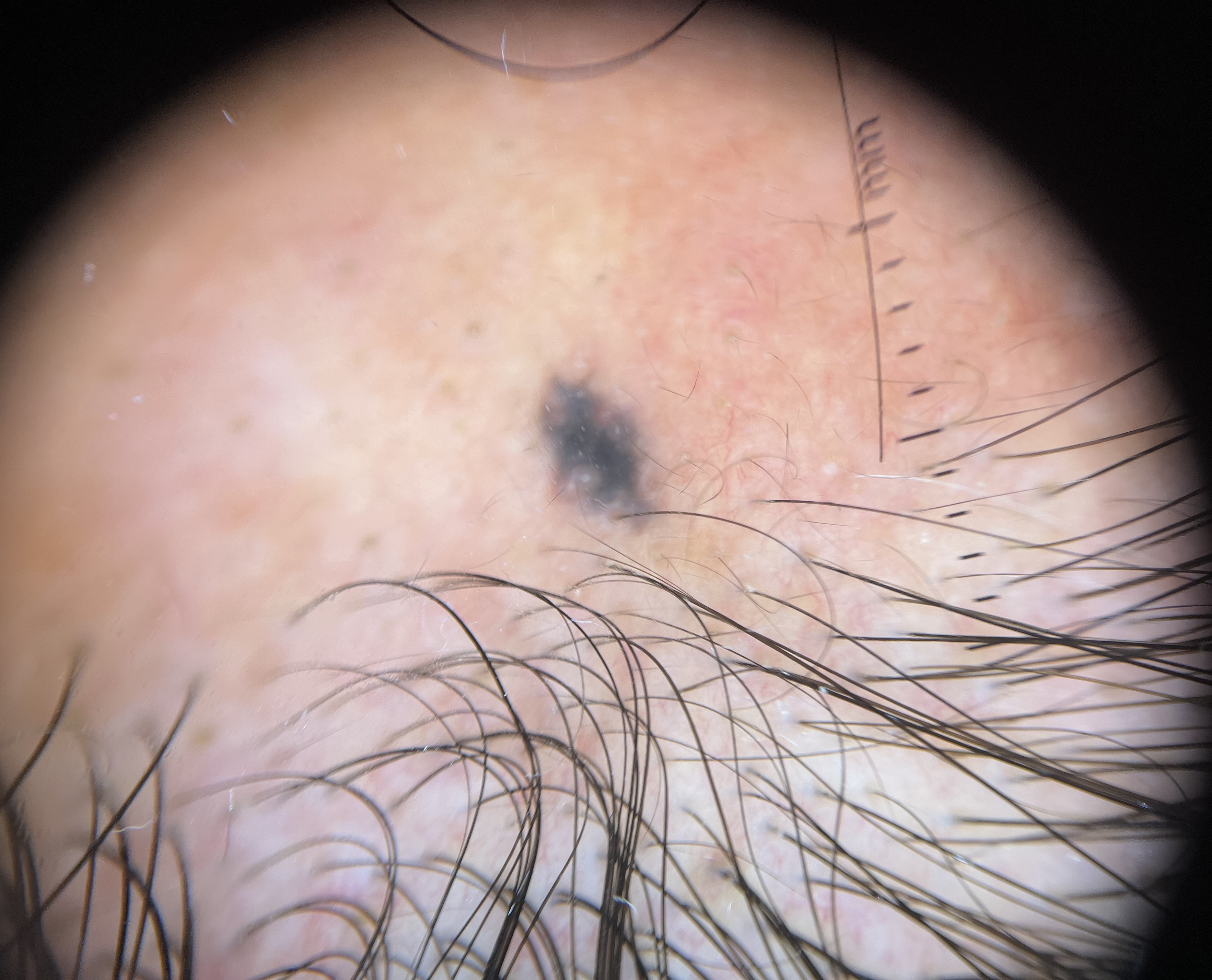Q: What is the imaging modality?
A: dermoscopy
Q: What is the lesion category?
A: banal, dermal
Q: What was the diagnostic impression?
A: blue nevus (expert consensus)